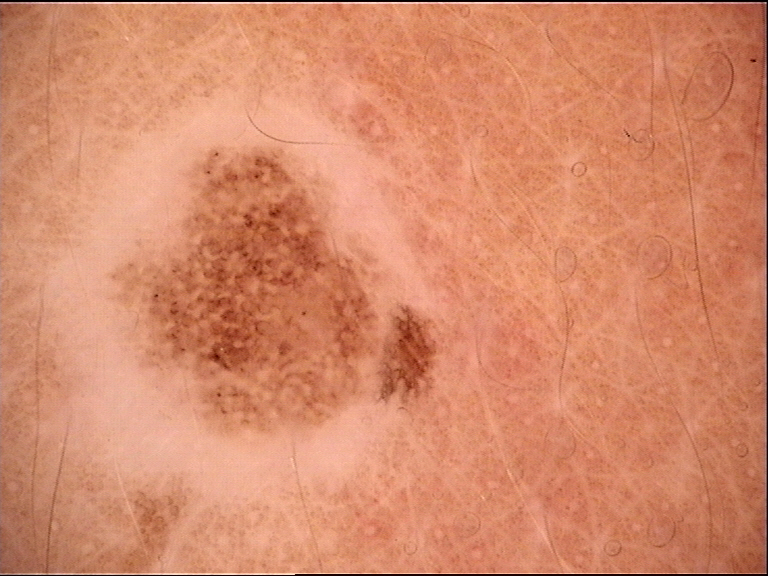Case:
- image type: dermatoscopy
- classification: banal
- diagnosis: junctional nevus (expert consensus)